A clinical photo of a skin lesion taken with a smartphone; Fitzpatrick phototype II; by history, alcohol use.
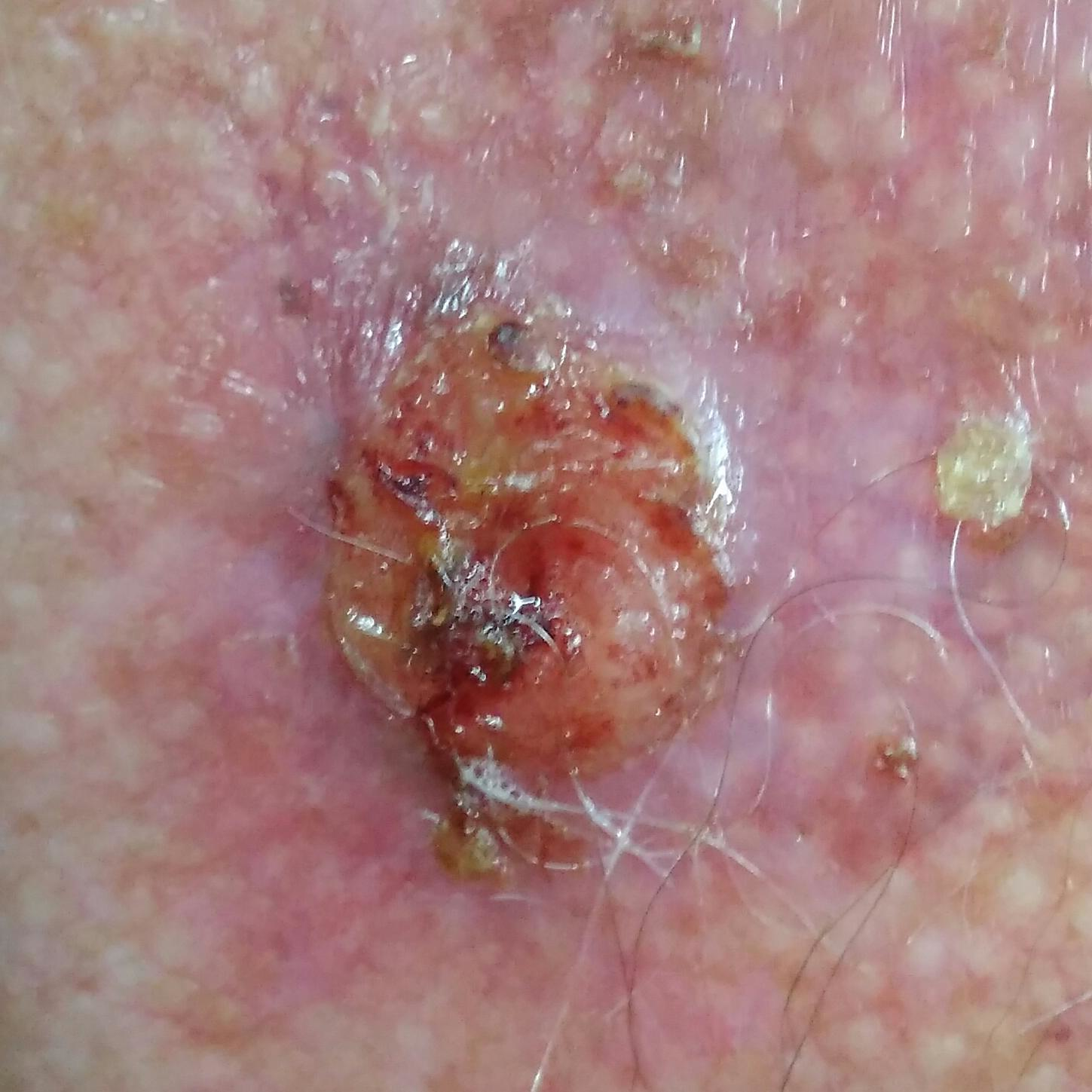Clinical context:
Located on the chest. The lesion is roughly 18 by 13 mm. The patient describes that the lesion has grown and is elevated.
Pathology:
The biopsy diagnosis was a malignancy — a squamous cell carcinoma.